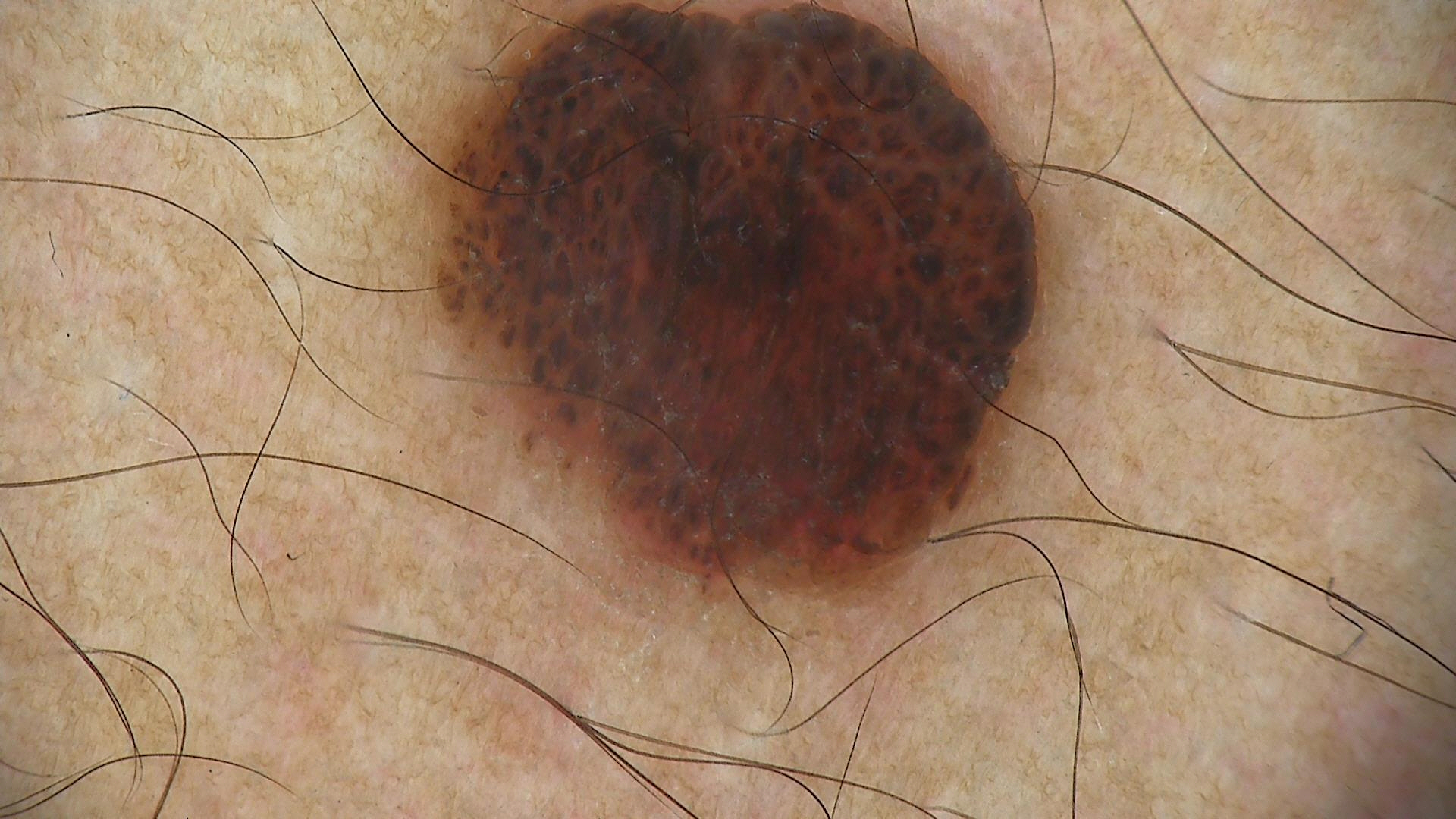Q: What kind of image is this?
A: dermatoscopy
Q: What is this lesion?
A: compound nevus (expert consensus)